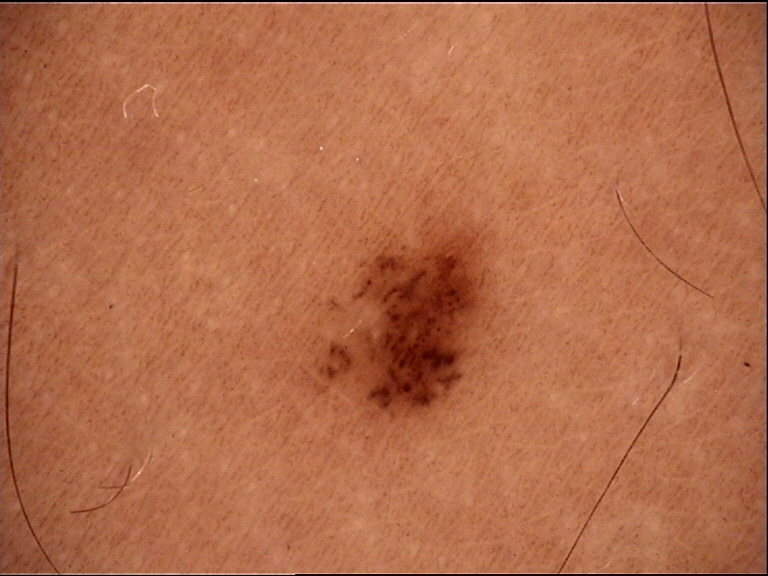imaging — dermoscopy
assessment — dysplastic junctional nevus (expert consensus)